Texture is reported as raised or bumpy · the photograph was taken at a distance · the subject is a female aged 60–69 · the arm is involved:
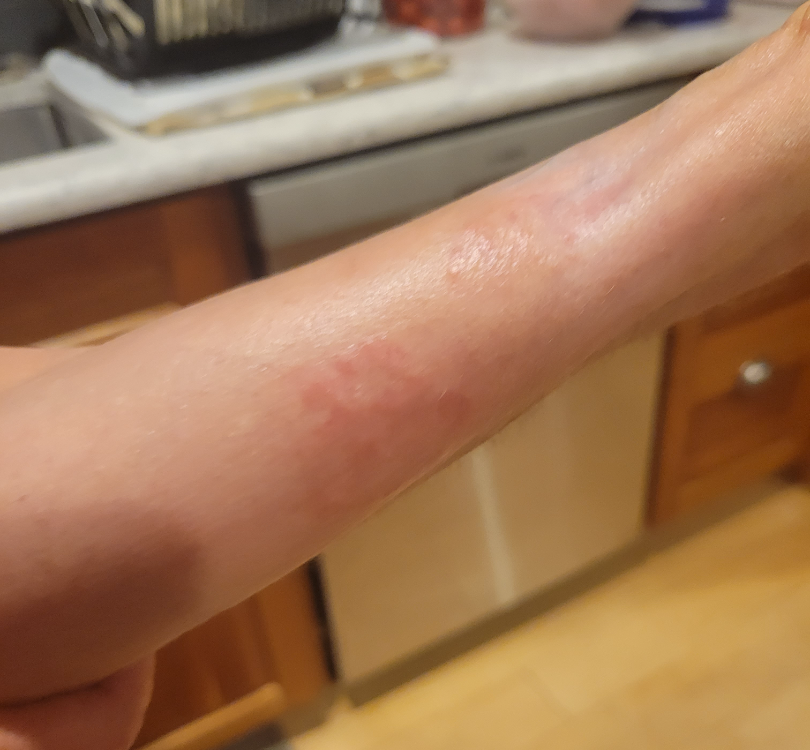dermatologist impression: the leading consideration is Granuloma annulare.